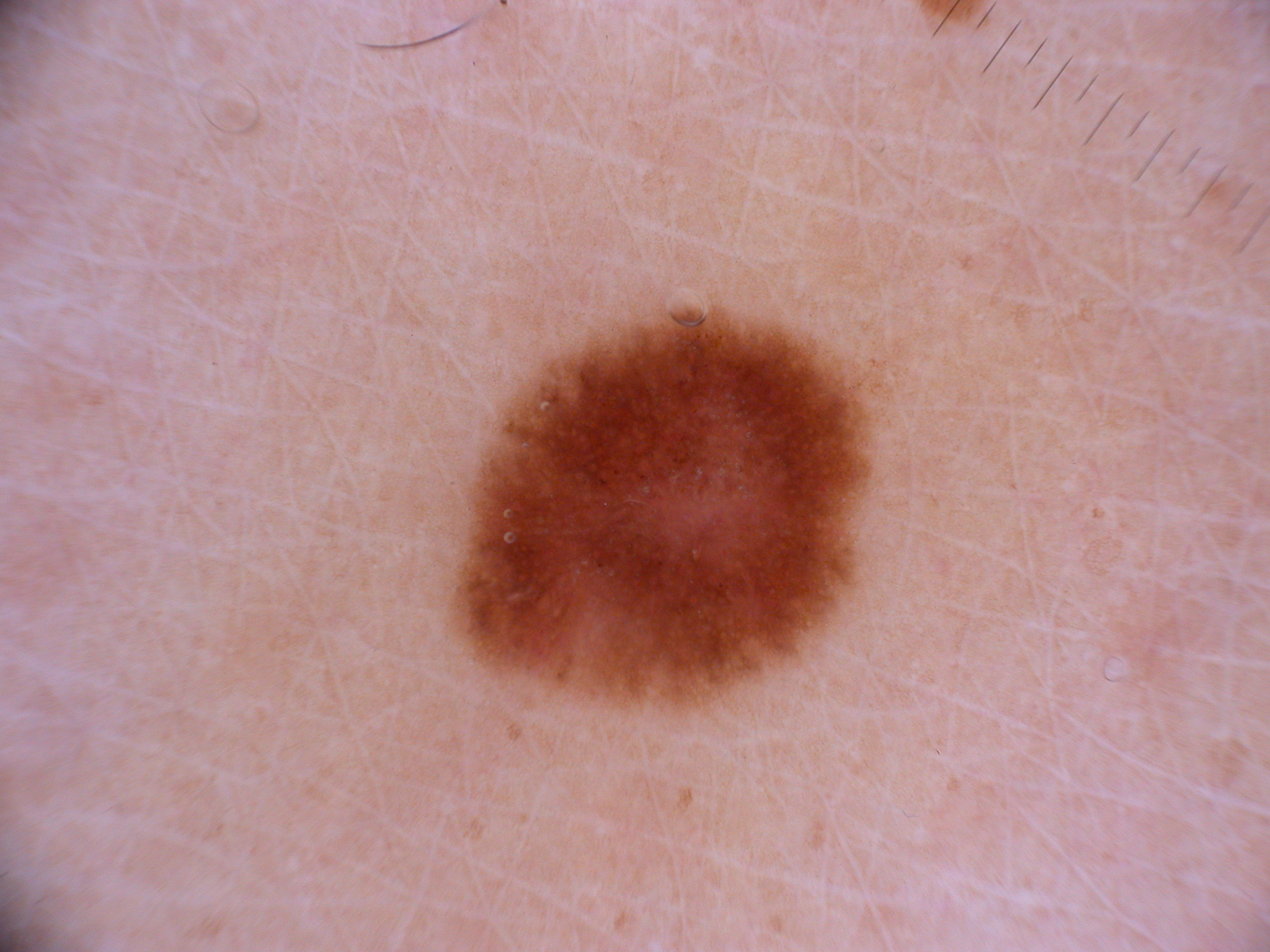Q: What is the imaging modality?
A: dermoscopy
Q: Where is the lesion in the image?
A: [451, 307, 871, 713]
Q: Which dermoscopic features were noted?
A: pigment network; absent: globules, negative network, milia-like cysts, and streaks
Q: What is the diagnosis?
A: a melanocytic nevus